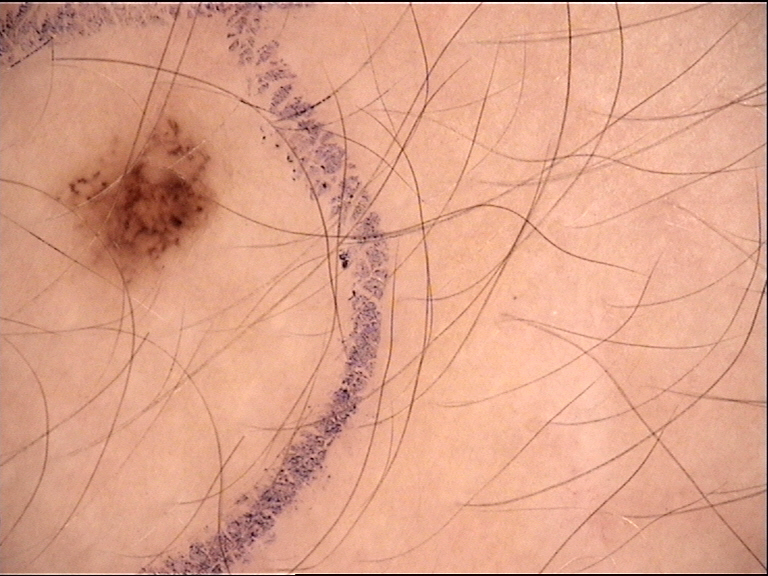Case:
• image type · dermoscopy
• diagnostic label · dysplastic junctional nevus (expert consensus)